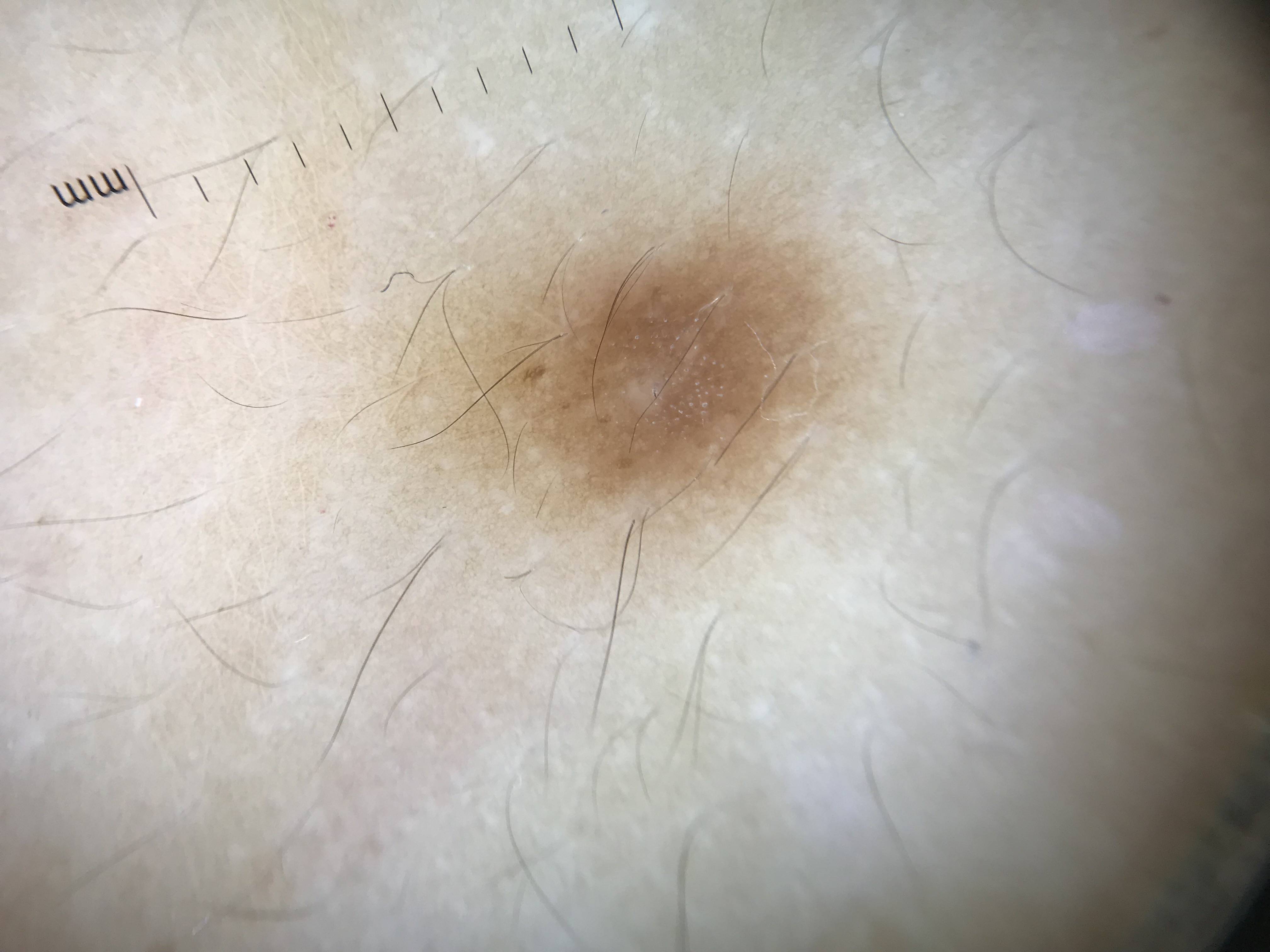Labeled as a benign lesion — a dermatofibroma.